Reported duration is one to four weeks; the photograph was taken at an angle; the patient notes the lesion is raised or bumpy; the lesion involves the front of the torso, back of the torso, arm and back of the hand; the subject is a female aged 50–59; self-categorized by the patient as a rash; the lesion is associated with itching, enlargement and bothersome appearance: 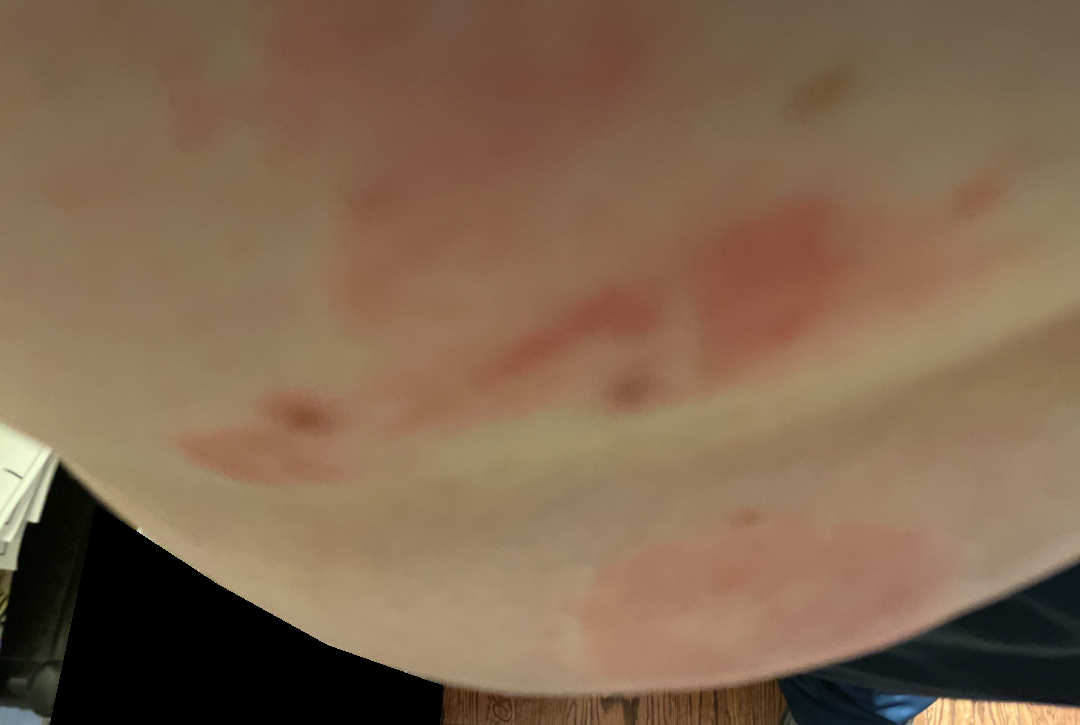The skin condition could not be confidently assessed from this image.